This image was taken at an angle: 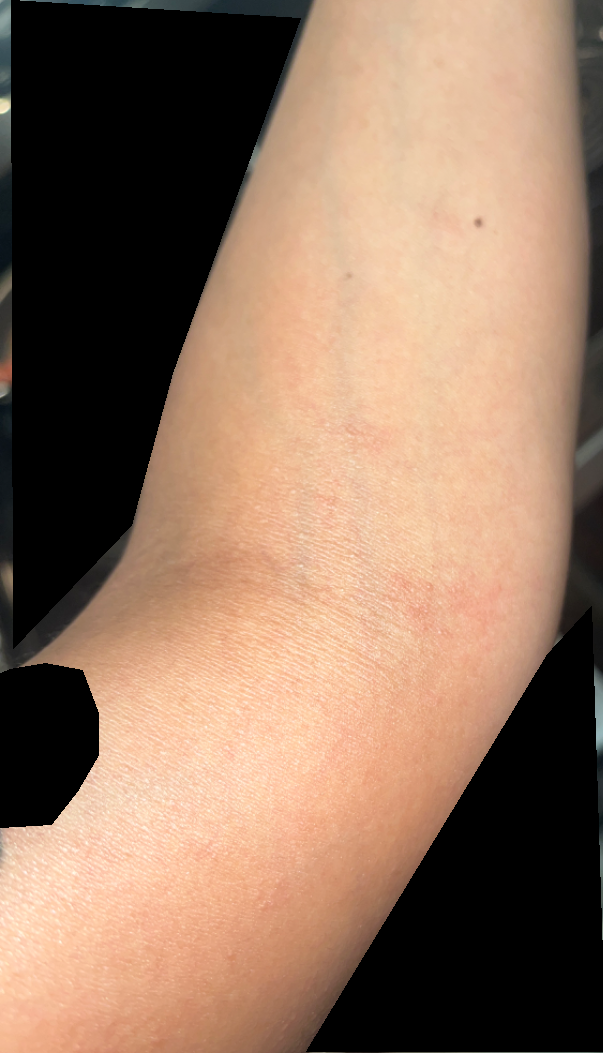Case summary:
– assessment — not assessable